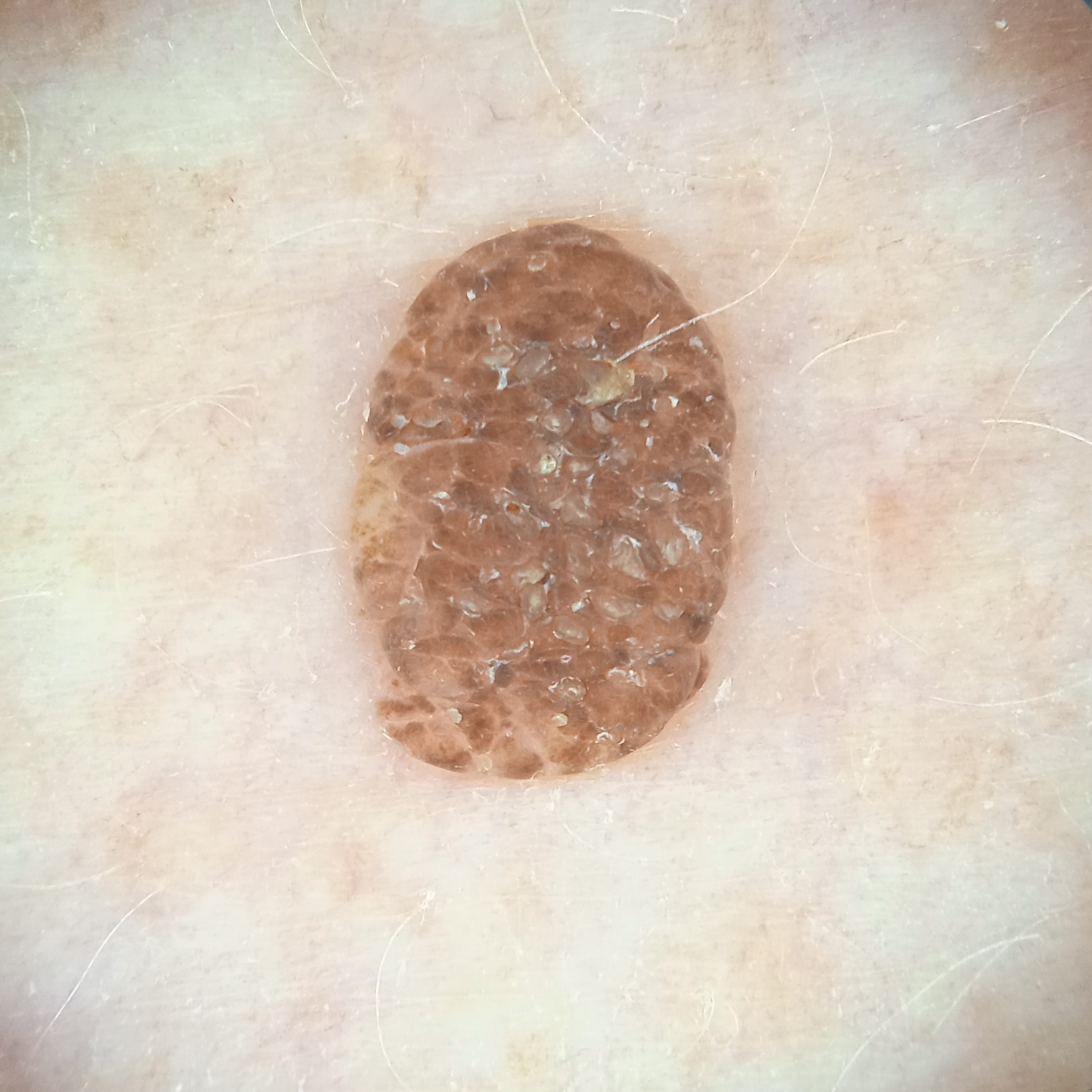  image: dermoscopic image
  referral: research study (no referral diagnosis)
  sun_reaction: skin tans without first burning
  mole_burden: numerous melanocytic nevi
  patient:
    age: 78
    sex: female
  lesion_location: an arm
  diagnosis:
    name: seborrheic keratosis
    malignancy: benign